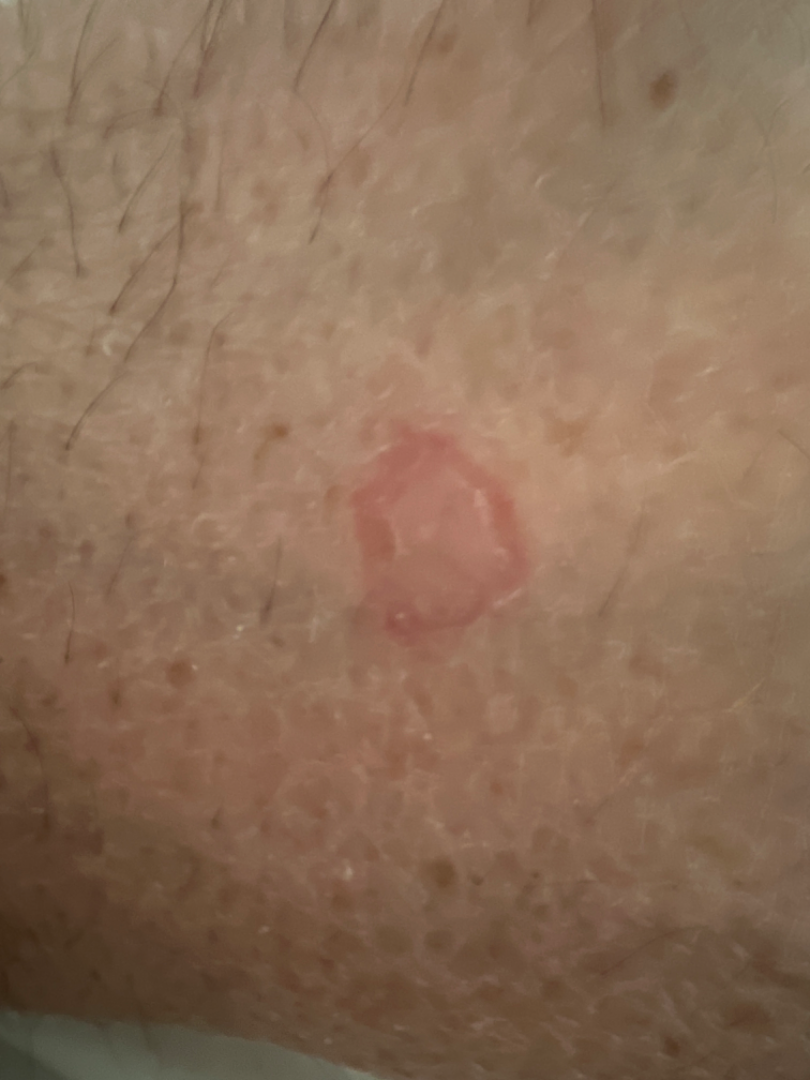• differential diagnosis · most likely Eczema; also raised was Tinea